A skin lesion imaged with a dermatoscope:
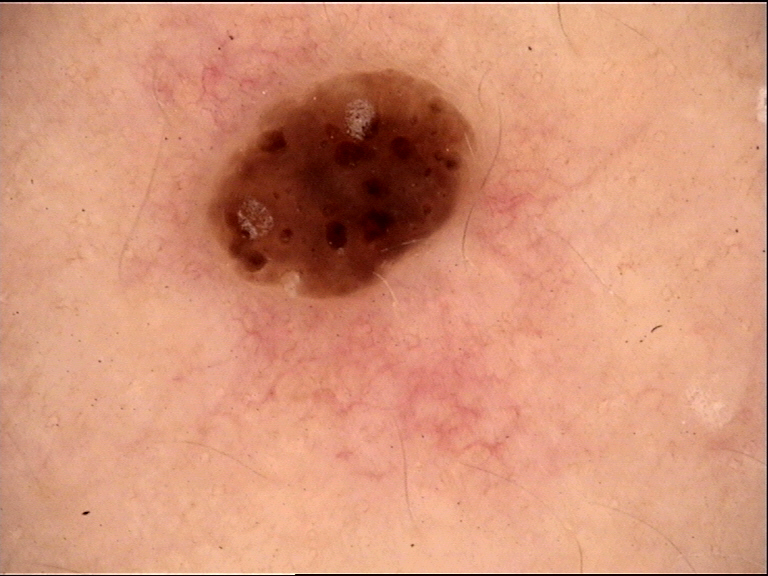The morphology is that of a keratinocytic lesion.
Classified as a seborrheic keratosis.